A dermoscopy image of a single skin lesion.
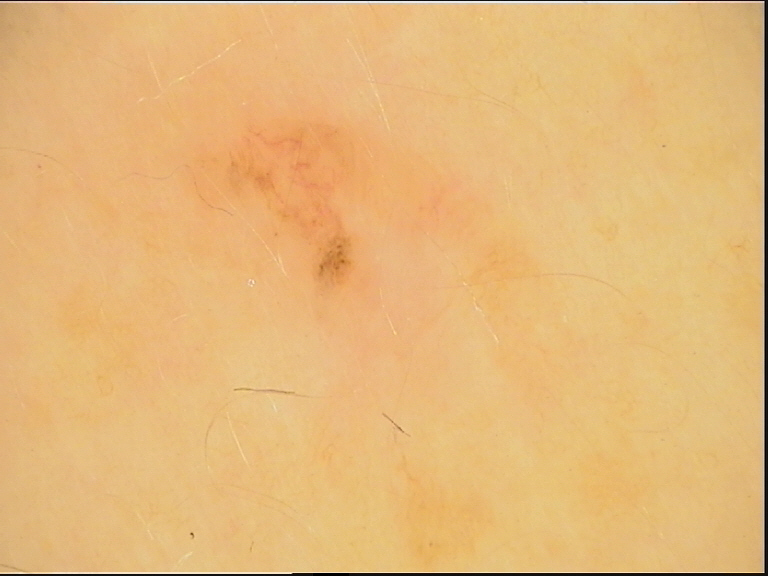Consistent with a dysplastic junctional nevus.